This is a close-up image · the lesion involves the palm and back of the hand · male subject, age 30–39:
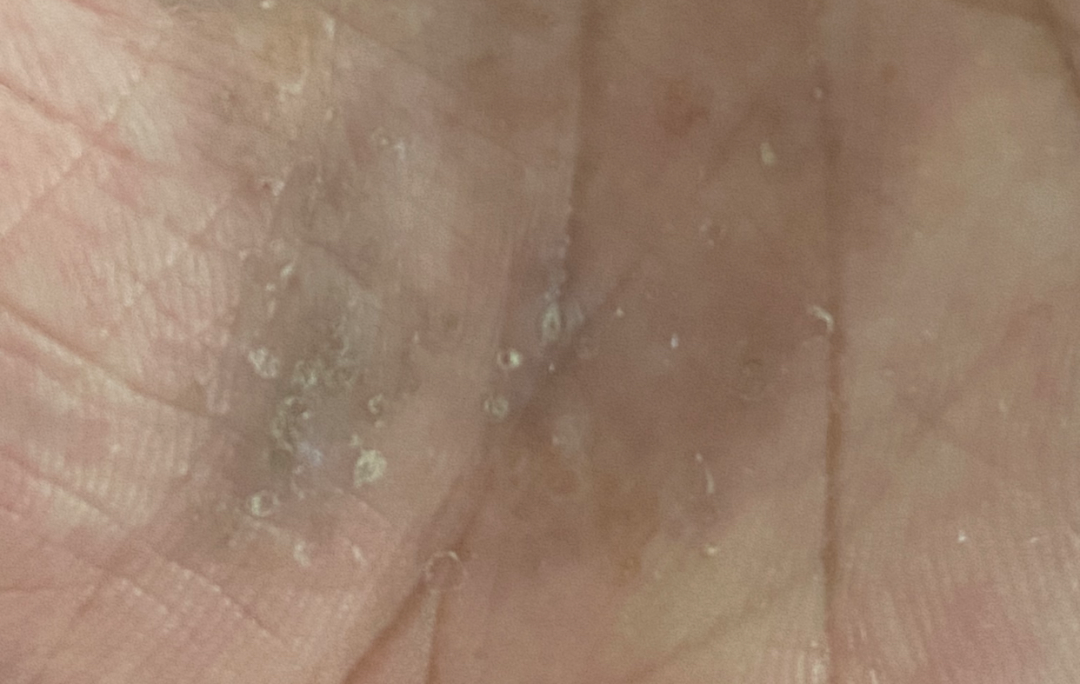{"differential": {"tied_lead": ["Tinea", "Keratoderma", "Chronic dermatitis, NOS"]}}